The patient describes having few moles overall; the patient reports no immunosuppression and no personal history of skin cancer; a male subject age 62; acquired for a research image collection, with no referral diagnosis:
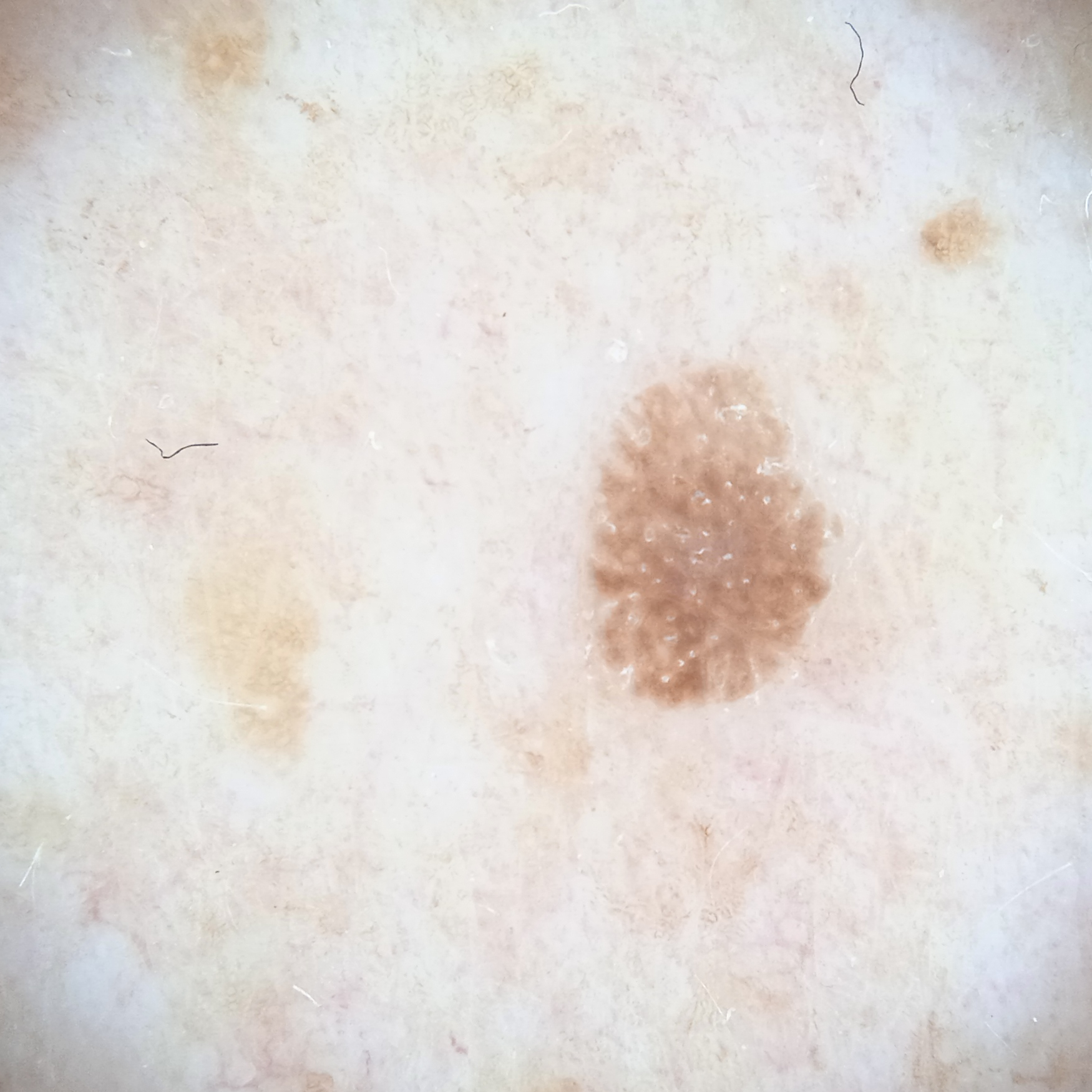{
  "lesion_location": "the back",
  "lesion_size": {
    "diameter_mm": 4.3
  },
  "diagnosis": {
    "name": "seborrheic keratosis",
    "malignancy": "benign"
  }
}